The chart records a prior melanoma. Dermoscopy of a skin lesion. Recorded as Fitzpatrick phototype II. A male patient aged around 85 or older — 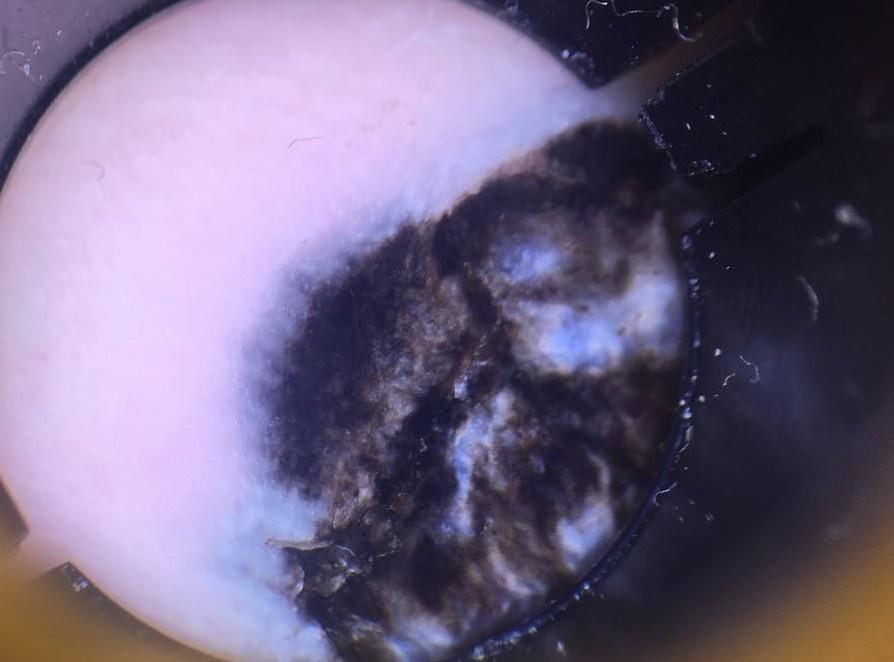The lesion involves an acral site (palms or soles). Histopathologically confirmed as a melanoma.